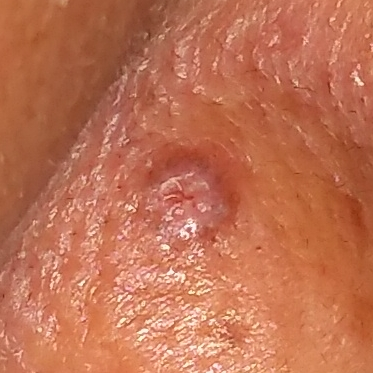A female patient age 55. A clinical photograph showing a skin lesion. The lesion was found on the nose. Per patient report, the lesion is elevated, but does not itch. The biopsy diagnosis was an actinic keratosis.